The leg is involved; female subject, age 50–59; no constitutional symptoms were reported; reported duration is three to twelve months; symptoms reported: enlargement, itching and bothersome appearance; self-categorized by the patient as a rash; the lesion is described as raised or bumpy; this image was taken at an angle.
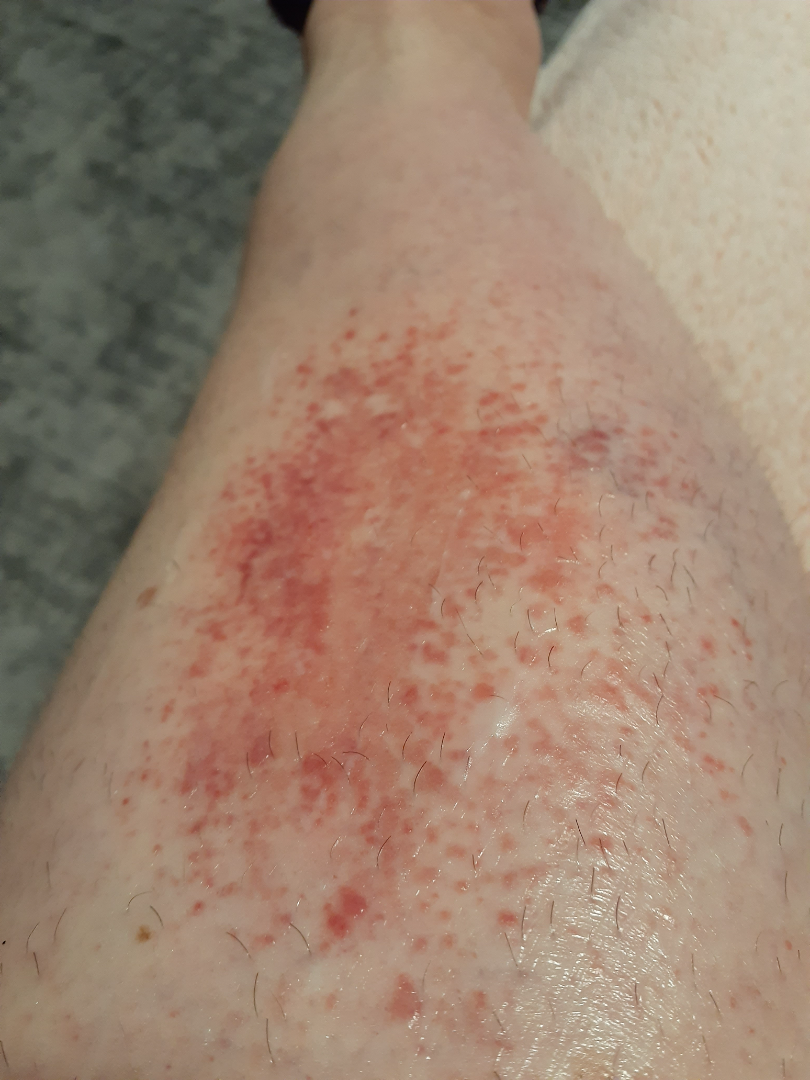On remote dermatologist review, Acute dermatitis, NOS (possible); Stasis Dermatitis (possible); Eczema (less likely); Burn of skin (less likely); Allergic Contact Dermatitis (less likely); Amyloidosis of skin (less likely).